Skin tone: FST III; human graders estimated Monk skin tone scale 2 or 4. This is a close-up image.
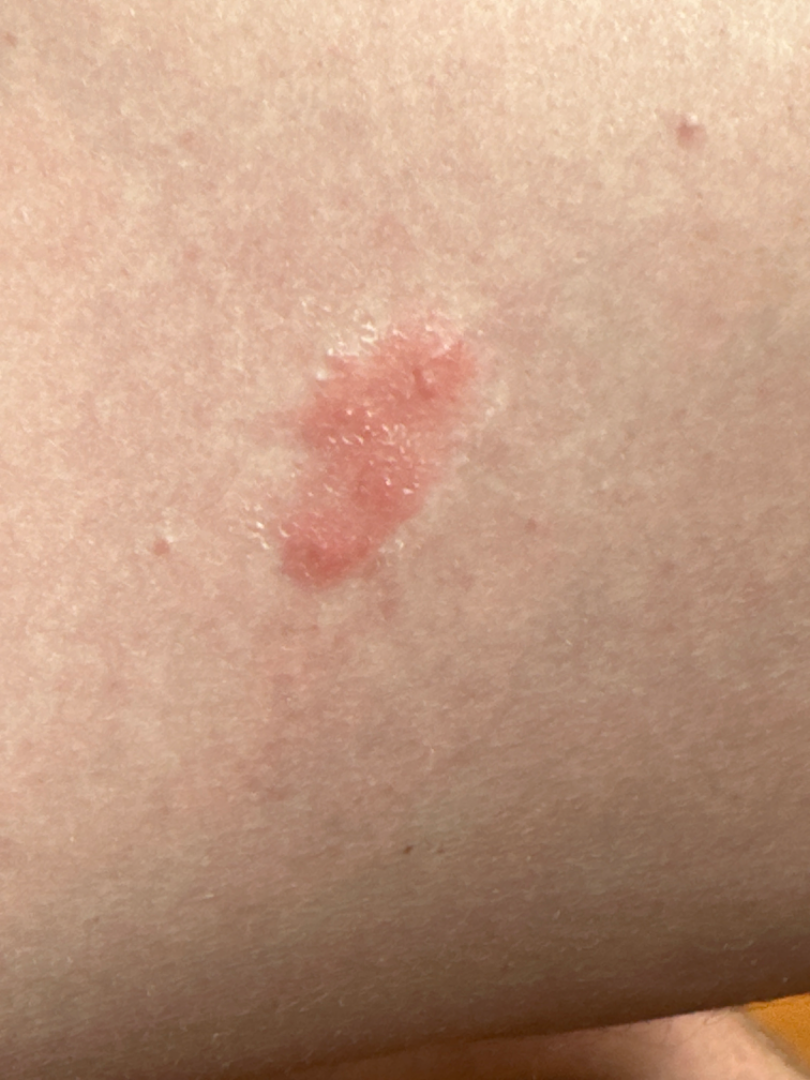The dermatologist could not determine a likely condition from the photograph alone.